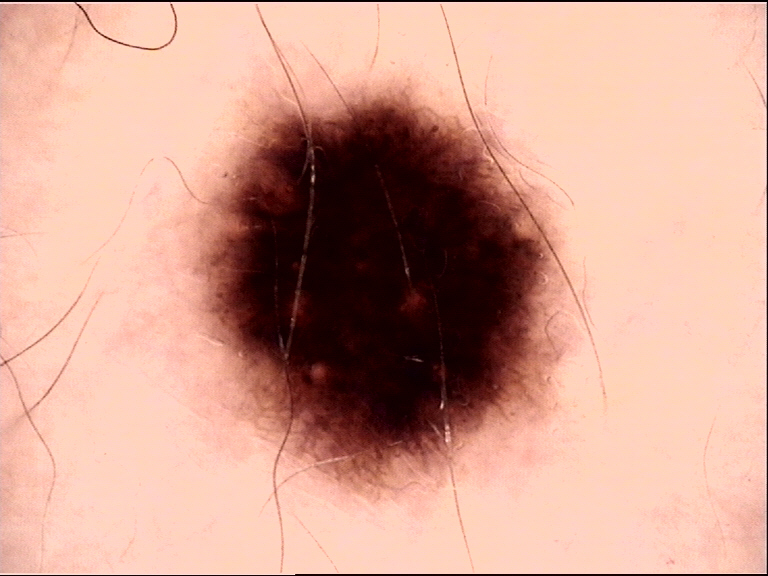Conclusion: The diagnostic label was a dysplastic junctional nevus.